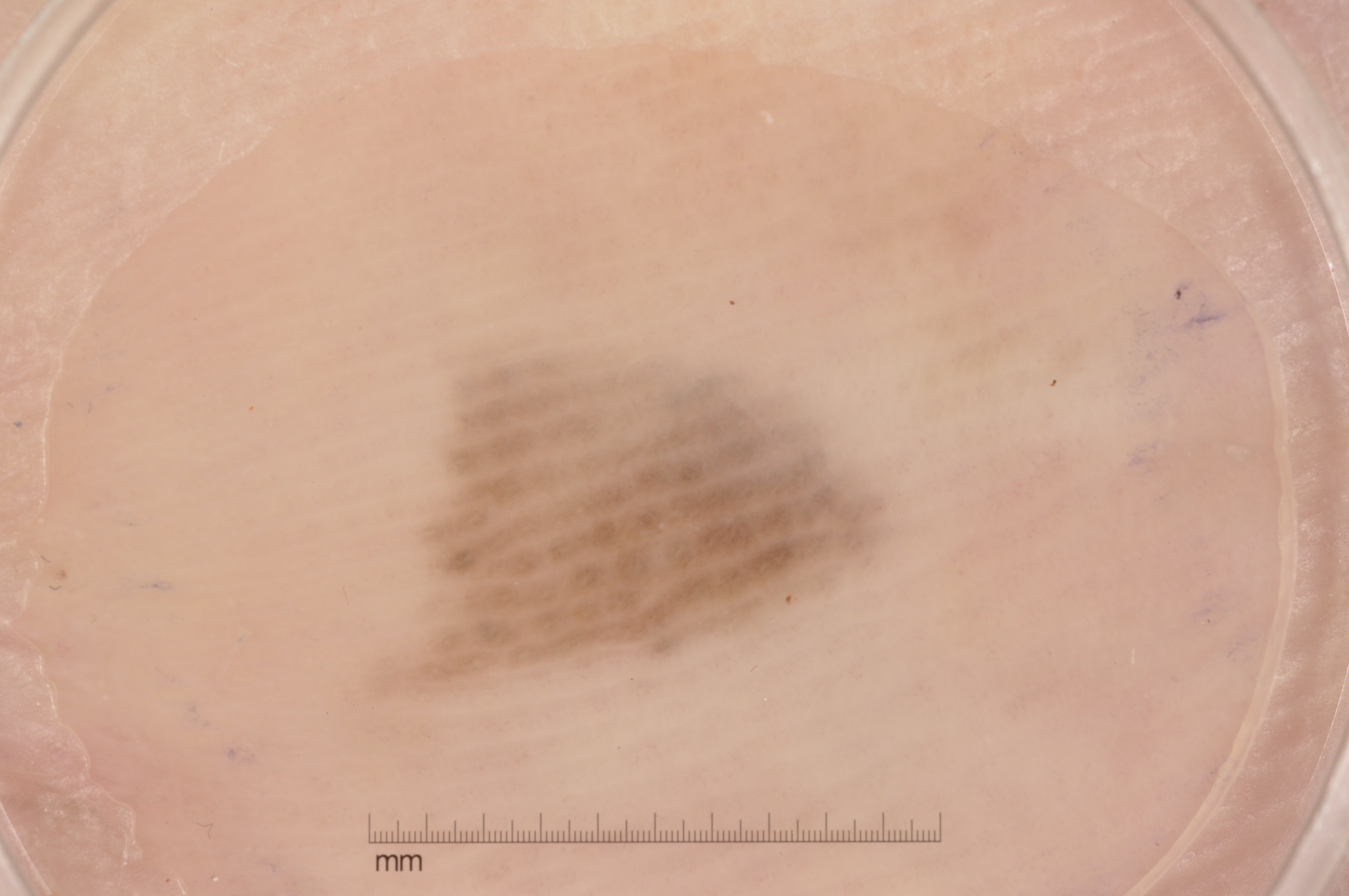Q: Patient demographics?
A: female, about 65 years old
Q: How was this image acquired?
A: dermoscopy of a skin lesion
Q: Which dermoscopic features are absent?
A: negative network, streaks, pigment network, and milia-like cysts
Q: How large is the lesion within the image?
A: ~8% of the field
Q: Where is the lesion located?
A: left=433, top=365, right=875, bottom=672
Q: What is the diagnosis?
A: a melanoma, a malignant skin lesion